A dermatoscopic image of a skin lesion: 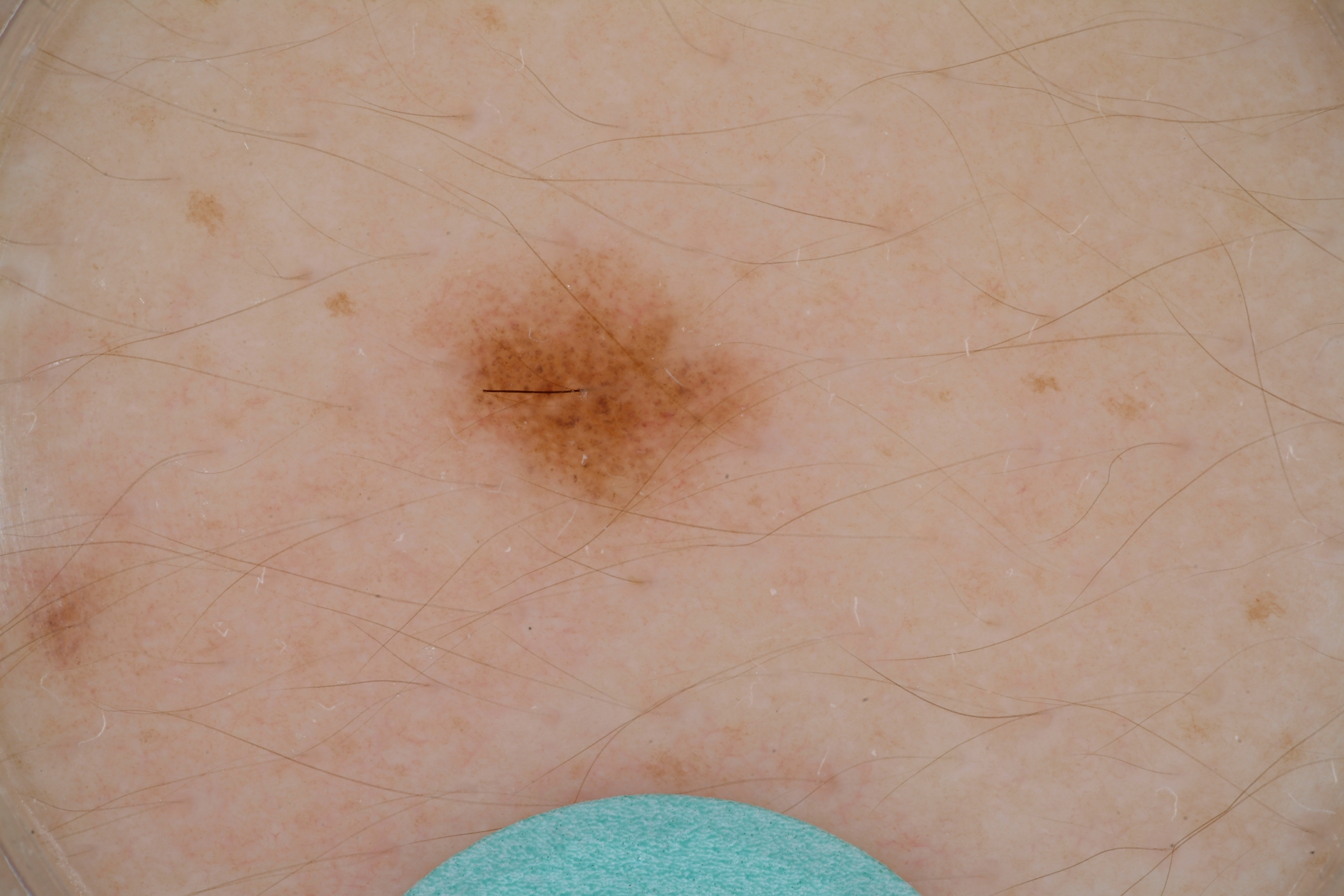extent = ~5% of the field | dermoscopic findings = globules; absent: streaks | location = bbox(425, 250, 775, 539) | impression = a benign skin lesion.